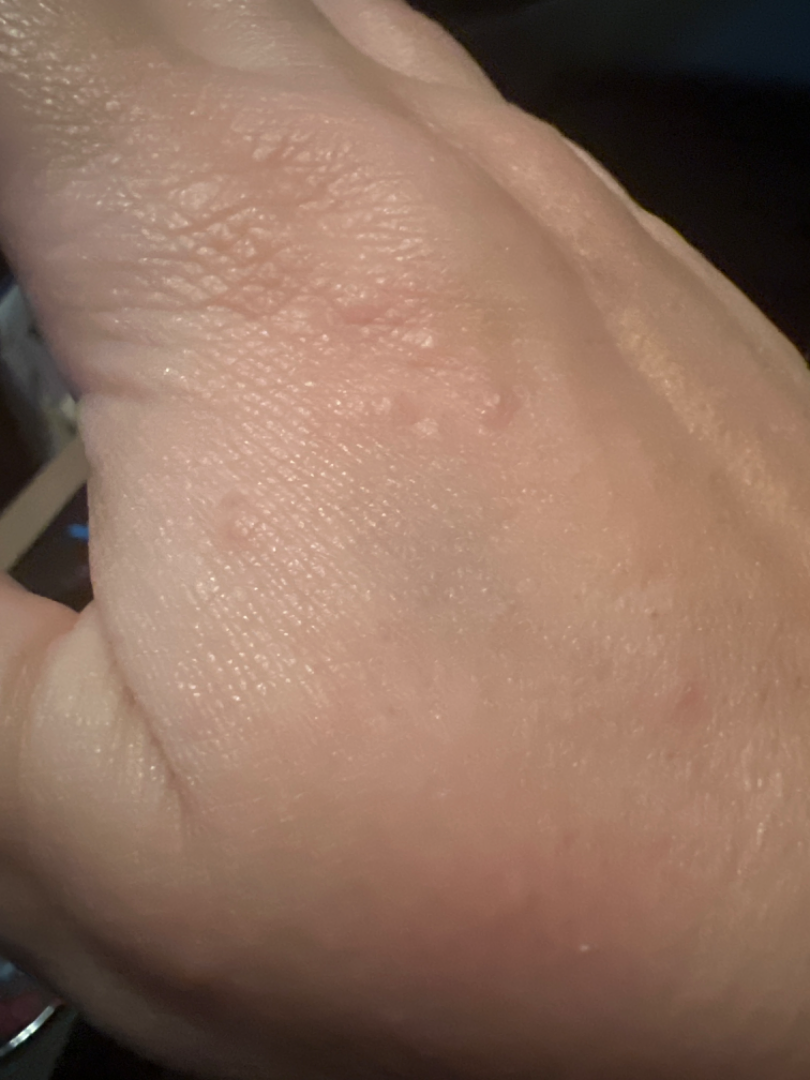assessment: could not be assessed
self-categorized as: skin that appeared healthy to them
described texture: raised or bumpy
present for: one to four weeks
lesion symptoms: itching and enlargement
shot type: close-up
anatomic site: back of the hand